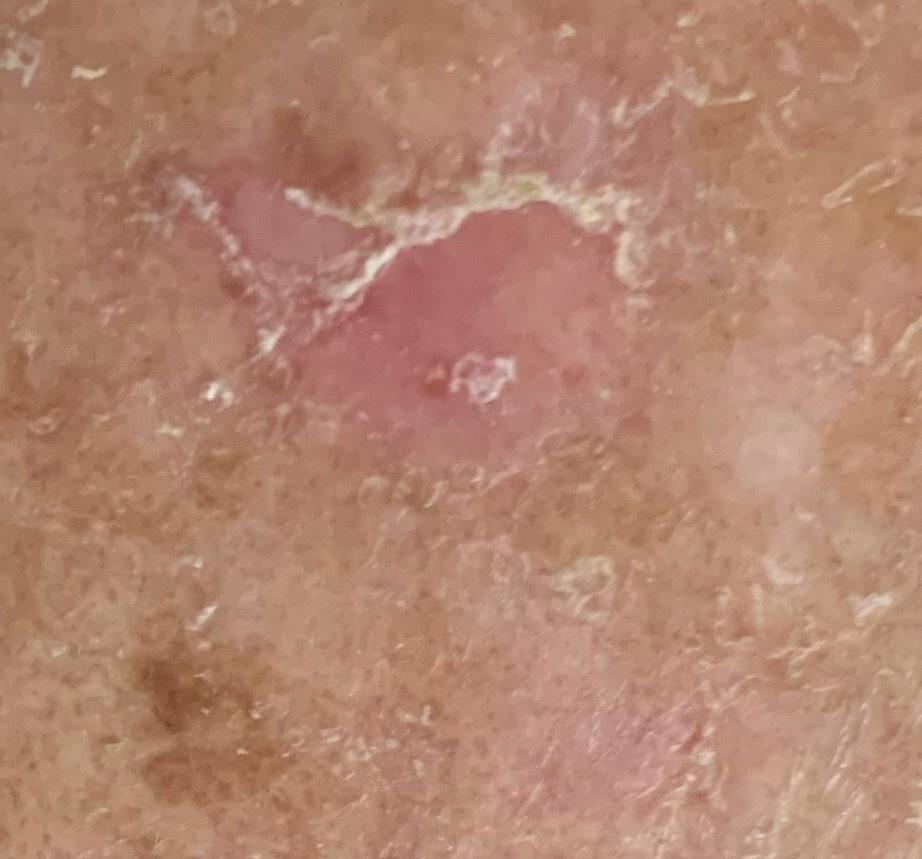A male patient aged 73-77.
A clinical overview photograph of a skin lesion.
Histopathologically confirmed as a solar or actinic keratosis.